The affected area is the leg. An image taken at a distance.
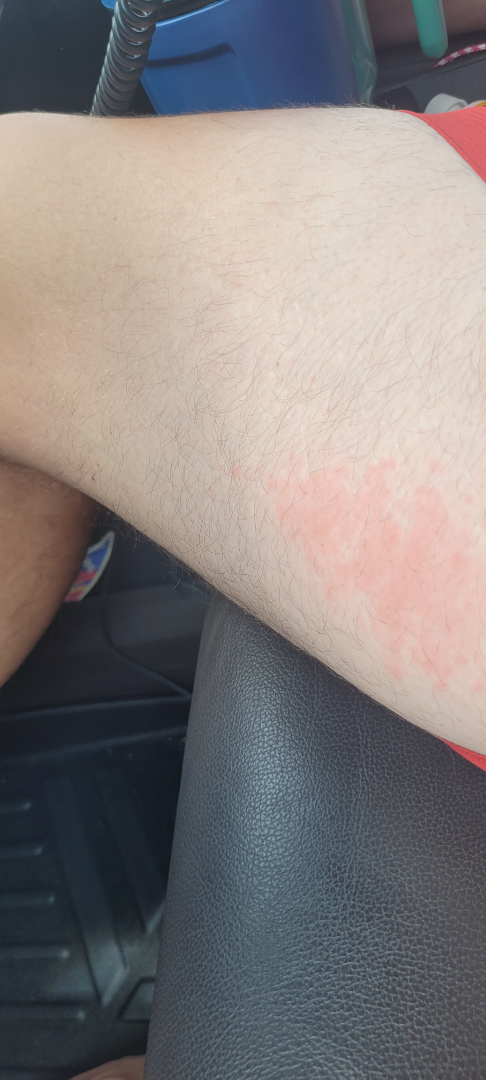<summary>
  <assessment>ungradable on photographic review</assessment>
</summary>